Reported duration is about one day. The patient reports itching and bothersome appearance. Texture is reported as raised or bumpy and flat. The lesion involves the back of the hand. This image was taken at an angle. The patient reports associated fatigue. Female subject, age 18–29: 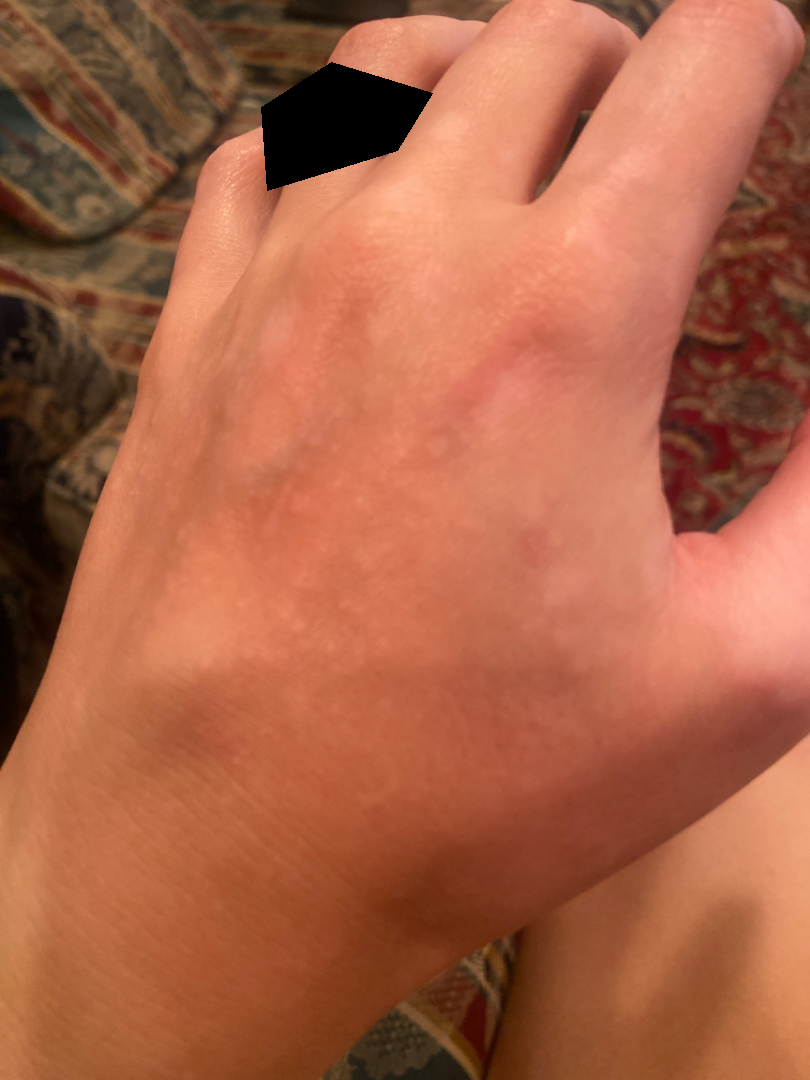On remote dermatologist review, most likely Post-Inflammatory hypopigmentation; with consideration of Vitiligo.